The photo was captured at an angle · the back of the hand is involved — 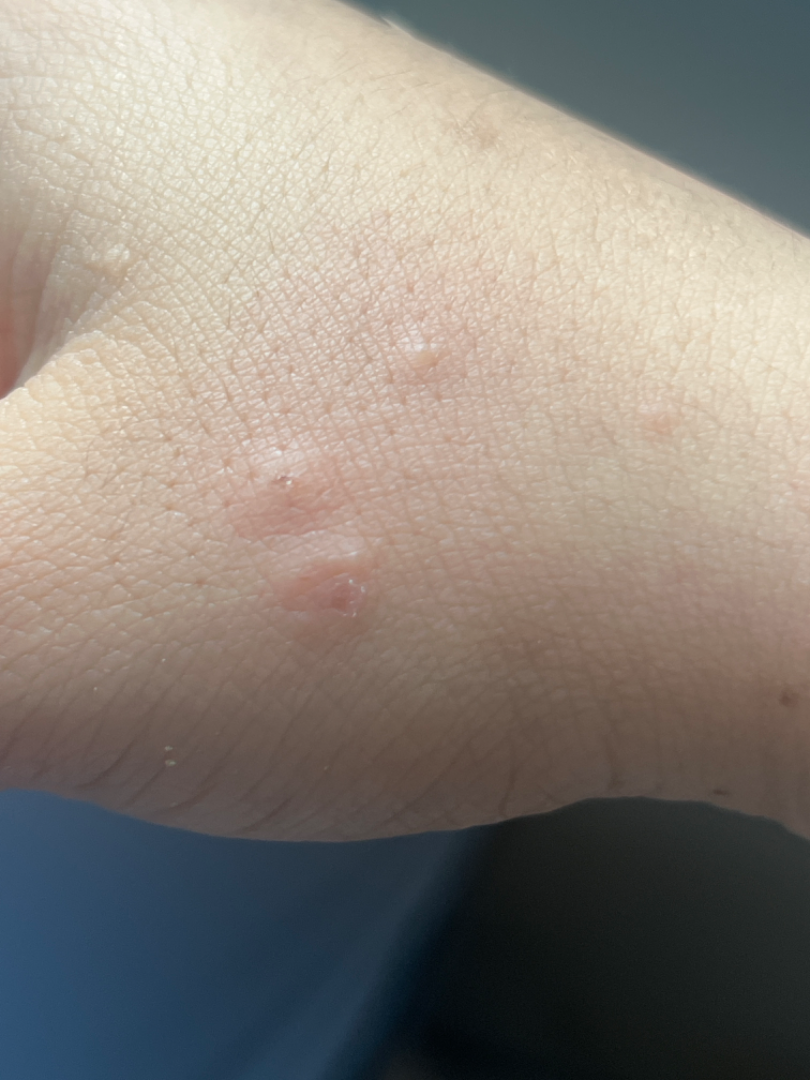Reported duration is less than one week. Self-categorized by the patient as skin that appeared healthy to them. The lesion is described as raised or bumpy. The lesion is associated with itching. Single-reviewer assessment: the differential includes Urticaria and Insect Bite, with no clear leading consideration.